The chart records prior malignancy (patient or family) and prior skin cancer (patient or family).
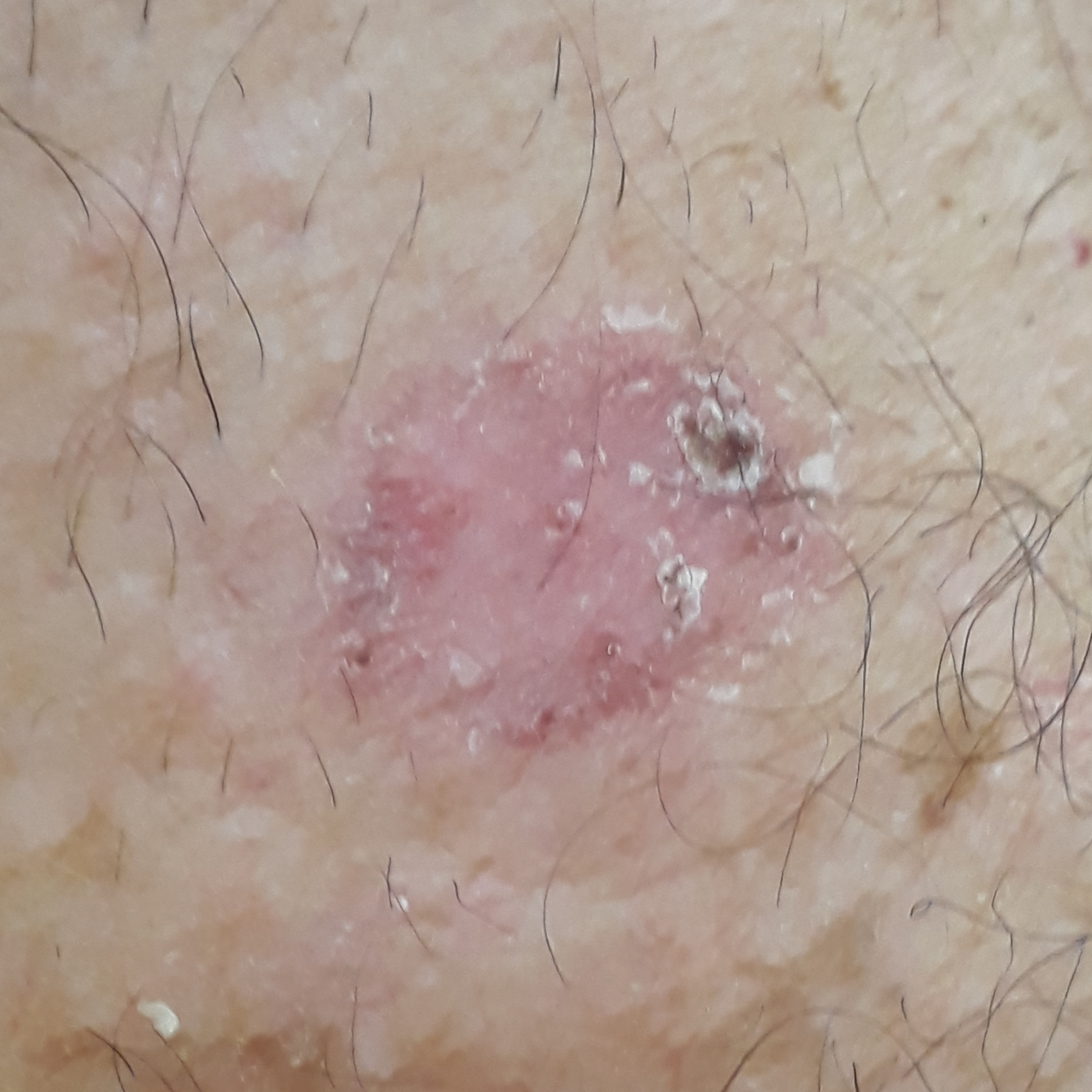<record>
<lesion_location>an arm</lesion_location>
<lesion_size>
<diameter_1_mm>17.0</diameter_1_mm>
<diameter_2_mm>11.0</diameter_2_mm>
</lesion_size>
<symptoms>none reported</symptoms>
<diagnosis>
<name>basal cell carcinoma</name>
<code>BCC</code>
<malignancy>malignant</malignancy>
<confirmation>histopathology</confirmation>
</diagnosis>
</record>